Male contributor, age 18–29; close-up view:
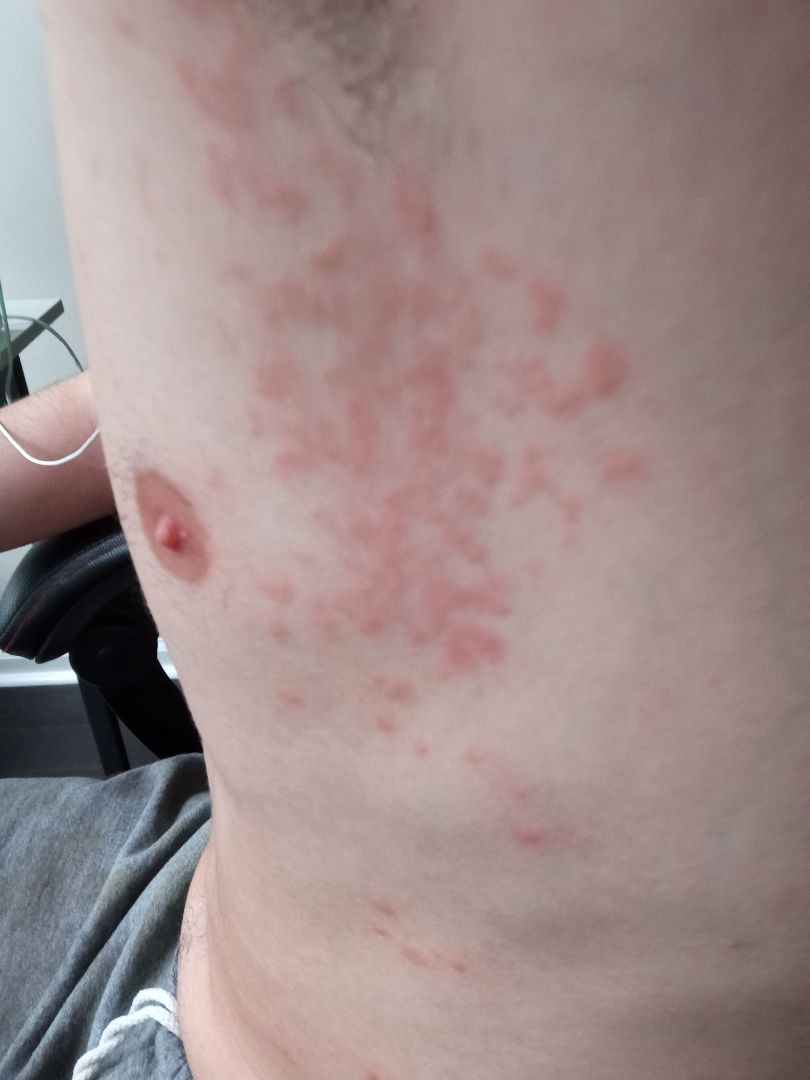Q: What was the assessment?
A: could not be assessed
Q: Reported symptoms?
A: itching and bothersome appearance
Q: What is the lesion texture?
A: raised or bumpy